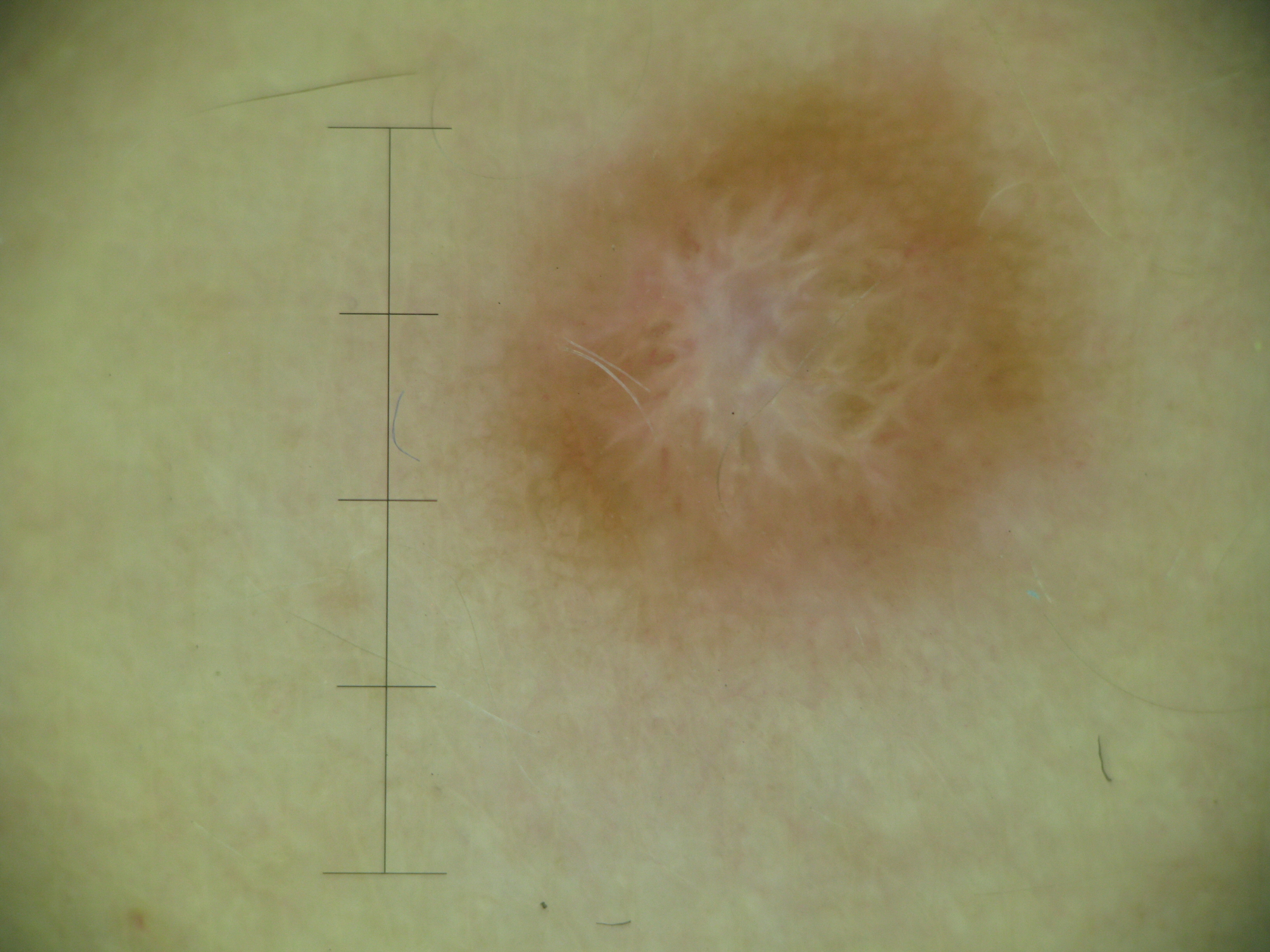Q: What kind of image is this?
A: dermoscopy
Q: What is the diagnosis?
A: dermatofibroma (expert consensus)